The patient is 18–29, female; close-up view: 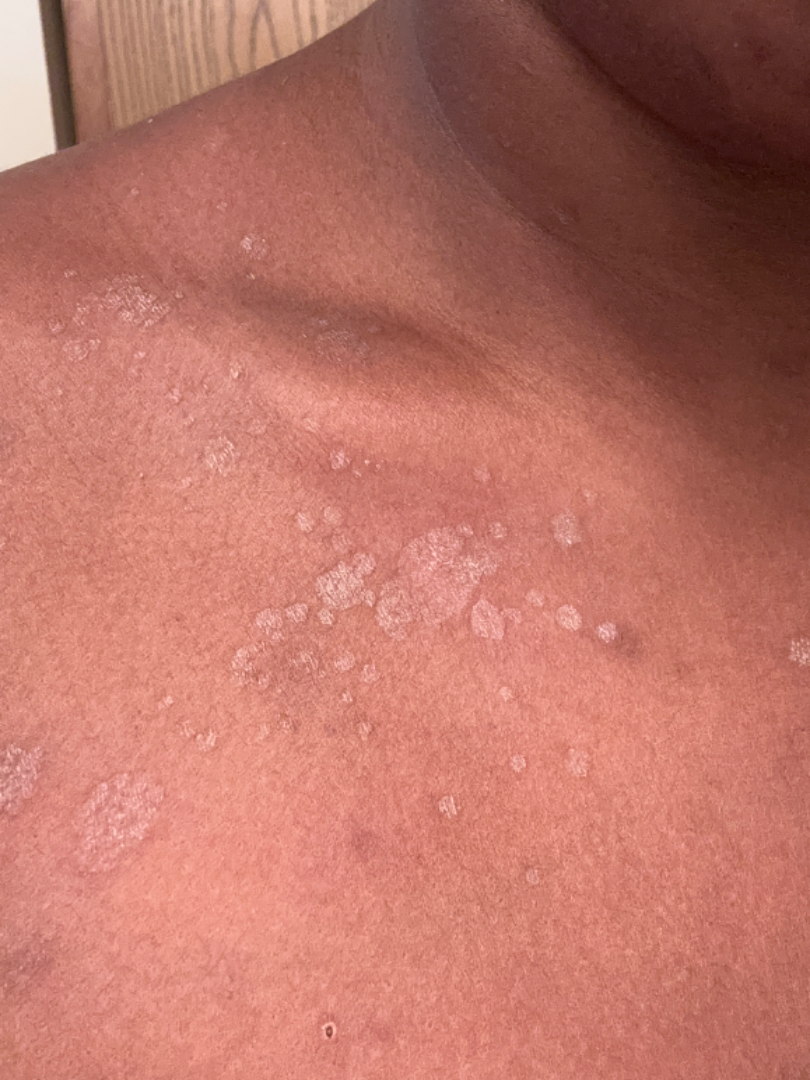Q: What conditions are considered?
A: one reviewing dermatologist: in keeping with Tinea Versicolor